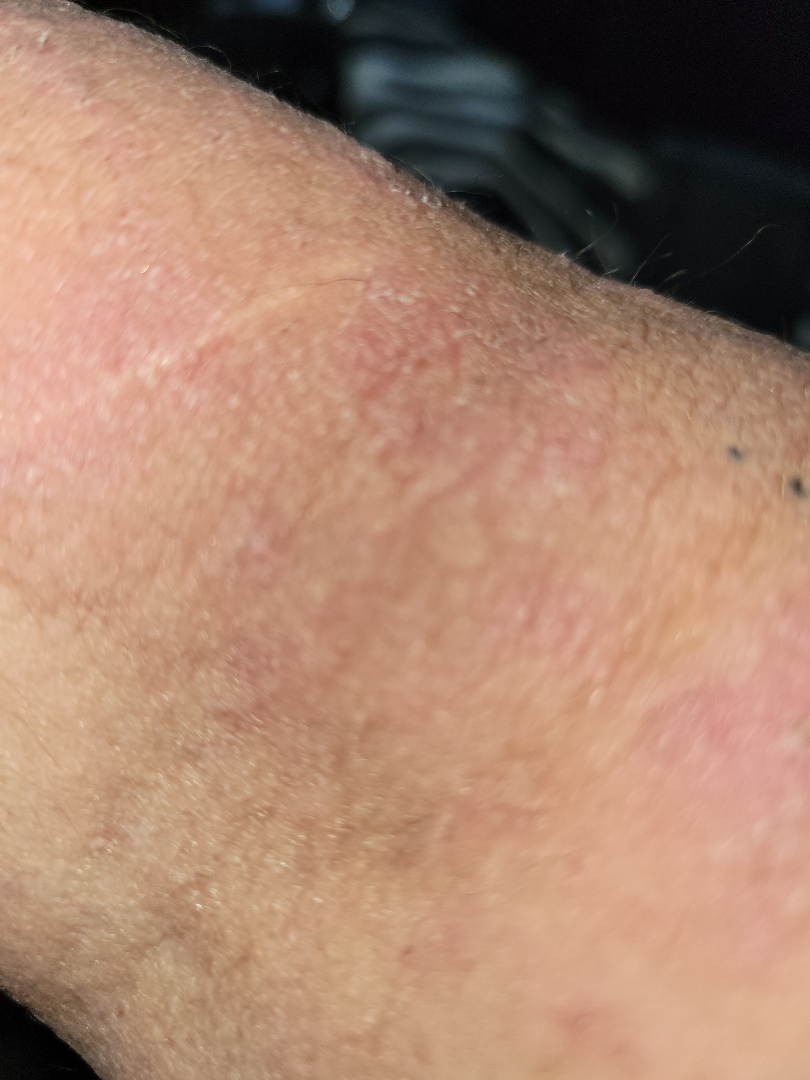The image was not sufficient for the reviewer to characterize the skin condition. Texture is reported as rough or flaky and raised or bumpy. The contributor reports the condition has been present for less than one week. This image was taken at an angle. Symptoms reported: itching, enlargement and bothersome appearance. Self-categorized by the patient as a rash. Female subject, age 50–59. The lesion involves the arm.